The subject is a female aged 60–69, a close-up photograph, the leg is involved.
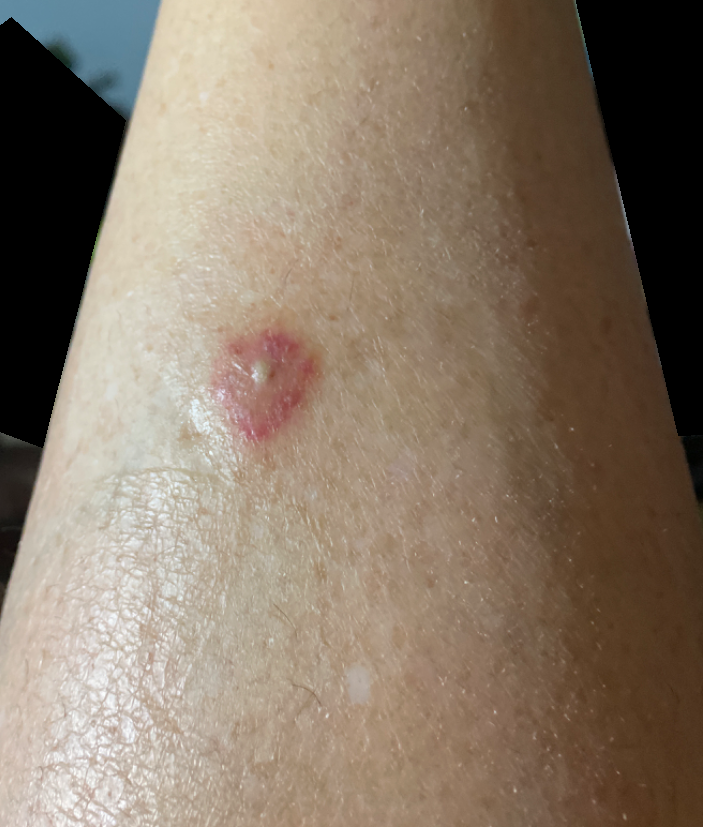patient describes the issue as: a rash; duration: less than one week; patient-reported symptoms: enlargement; described texture: fluid-filled and raised or bumpy; other reported symptoms: fatigue, mouth sores and joint pain; differential: consistent with Insect Bite.